The photograph was taken at a distance; the lesion involves the leg; the contributor is a female aged 70–79; texture is reported as raised or bumpy; reported lesion symptoms include pain, itching, bothersome appearance and enlargement; the patient described the issue as a rash; present for one to four weeks; no constitutional symptoms were reported — 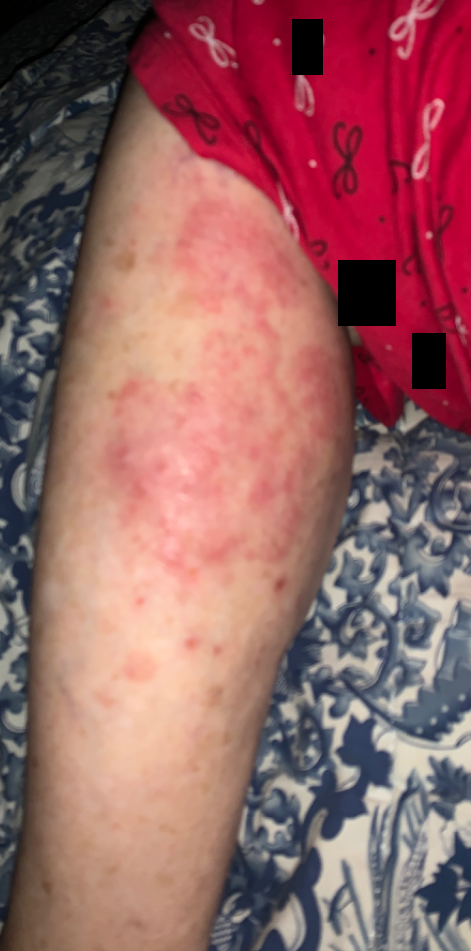Reviewed remotely by one dermatologist: the leading consideration is Tinea; also raised was Psoriasis; an alternative is Eczema.